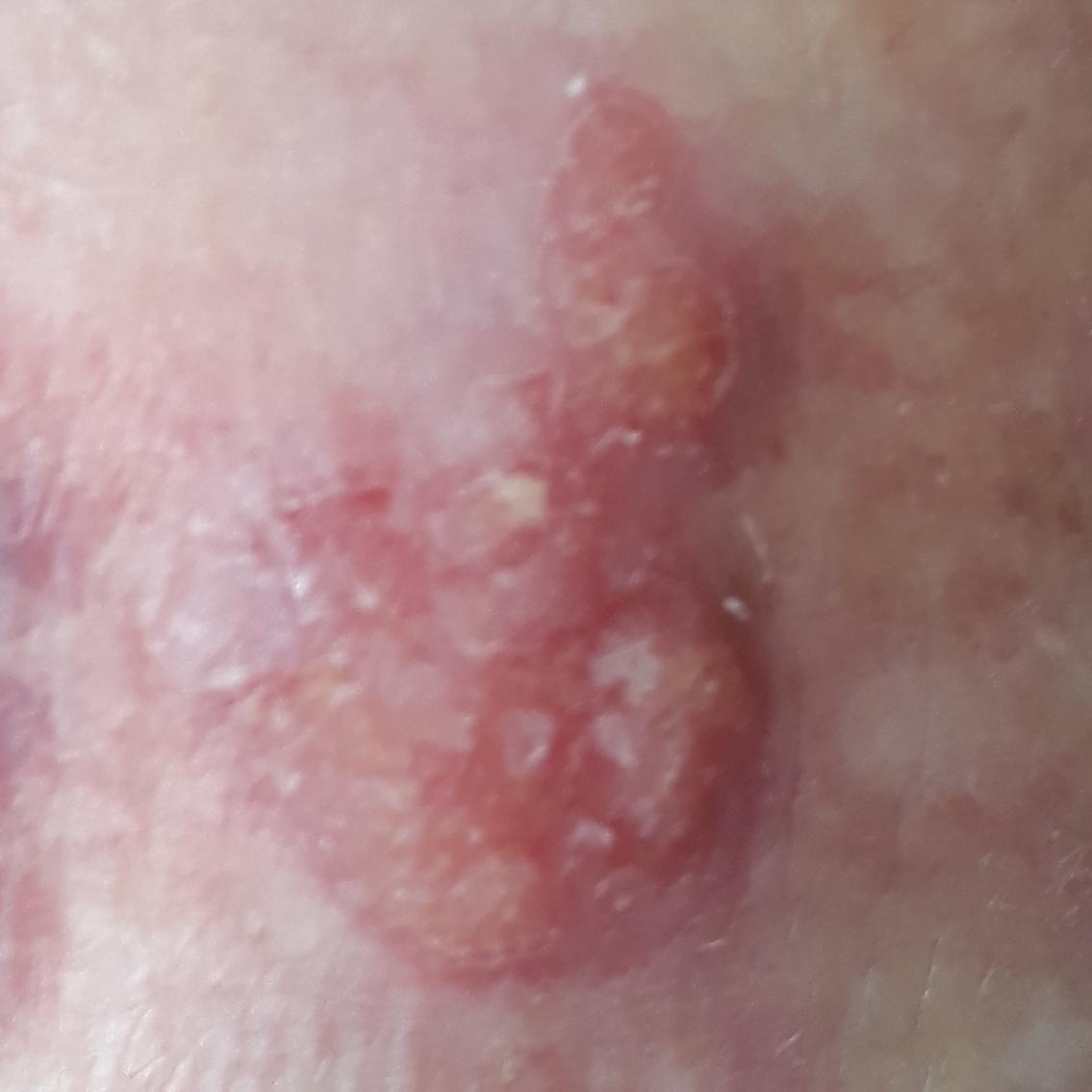diagnosis:
  name: squamous cell carcinoma
  code: SCC
  malignancy: malignant
  confirmation: histopathology